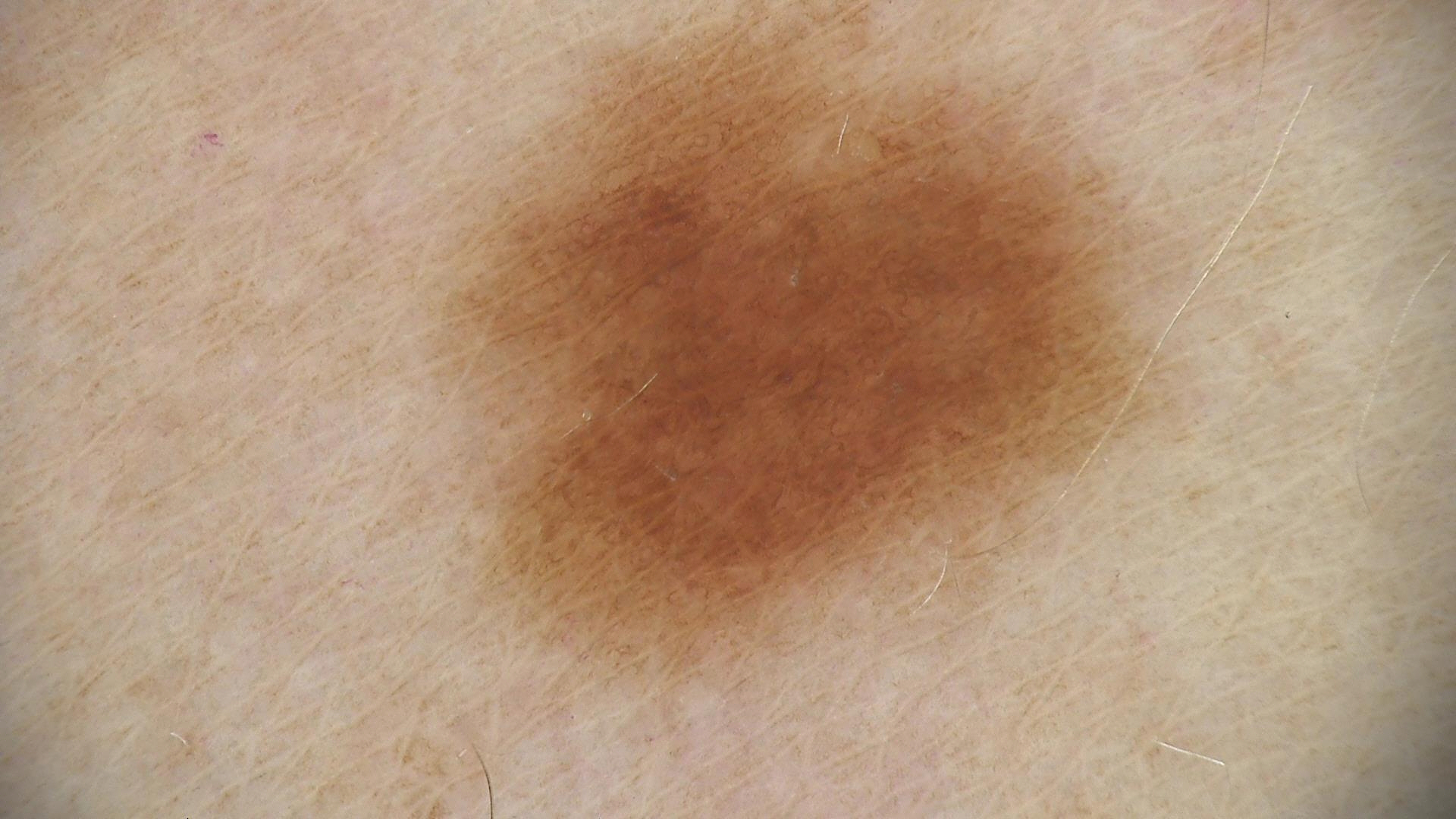Case:
* diagnosis: junctional nevus (expert consensus)